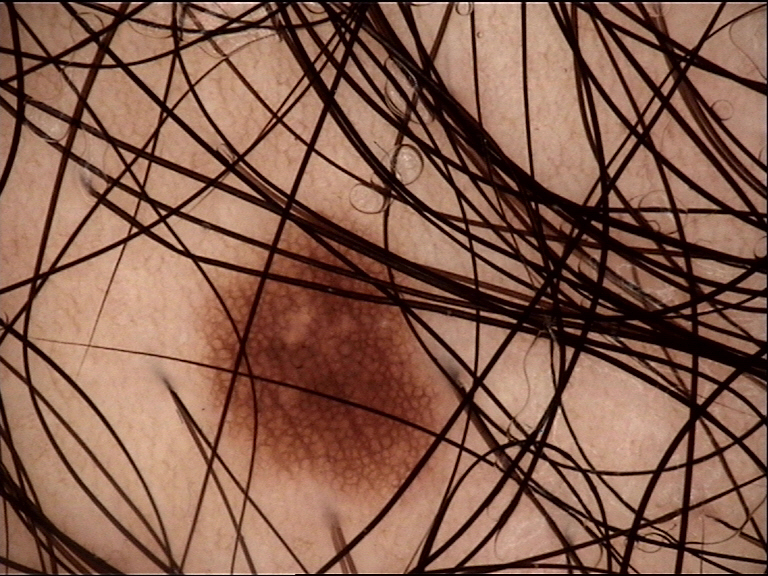Impression:
Consistent with a junctional nevus.